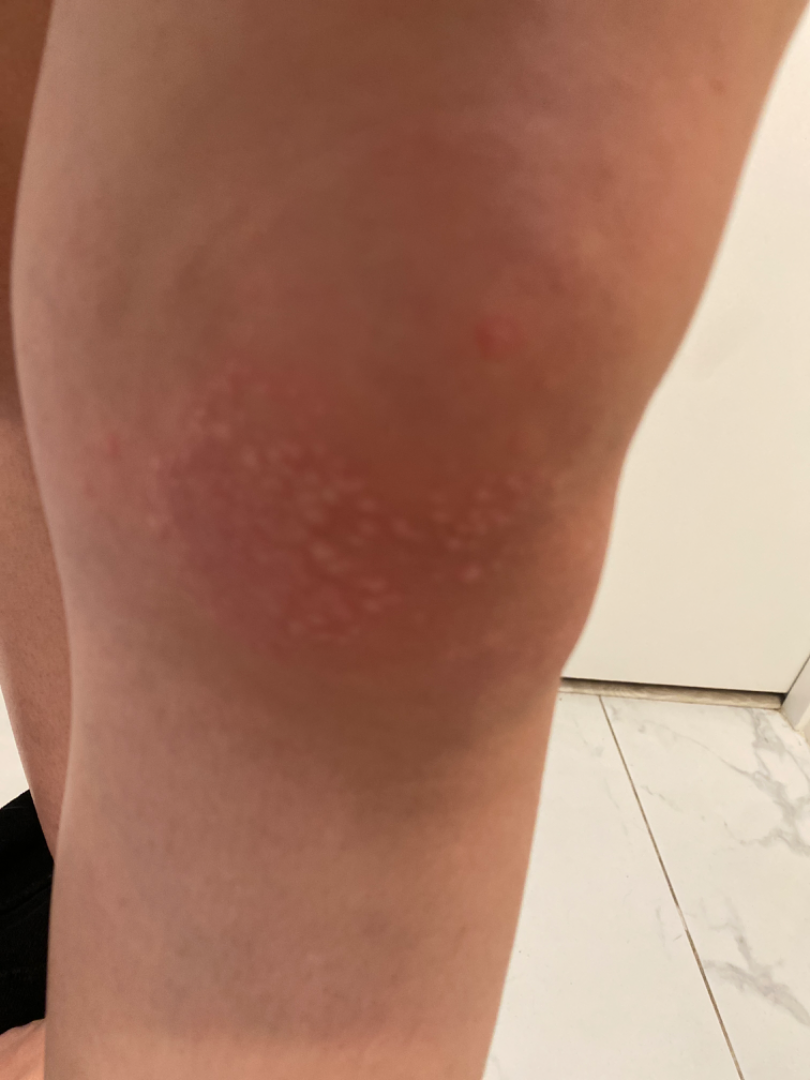Assessment: The favored diagnosis is Allergic Contact Dermatitis.